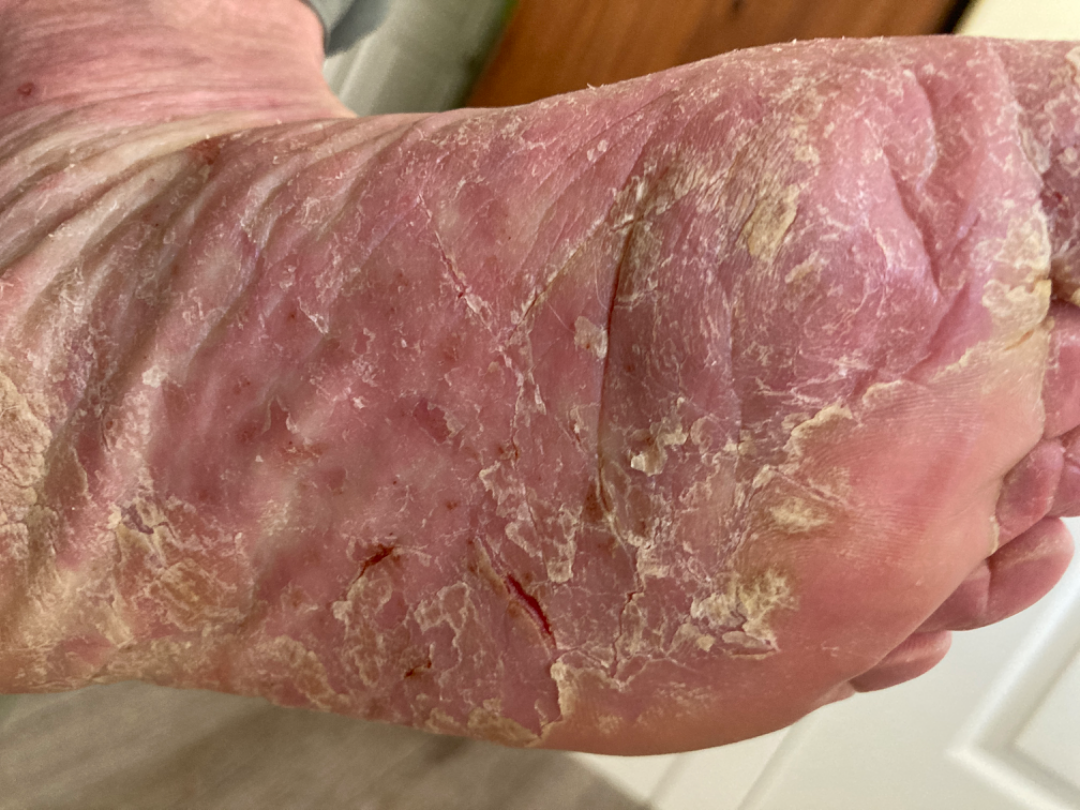<report>
<differential>
  <Psoriasis>0.41</Psoriasis>
  <Eczema>0.41</Eczema>
  <Tinea>0.18</Tinea>
</differential>
</report>